Dermoscopy of a skin lesion: 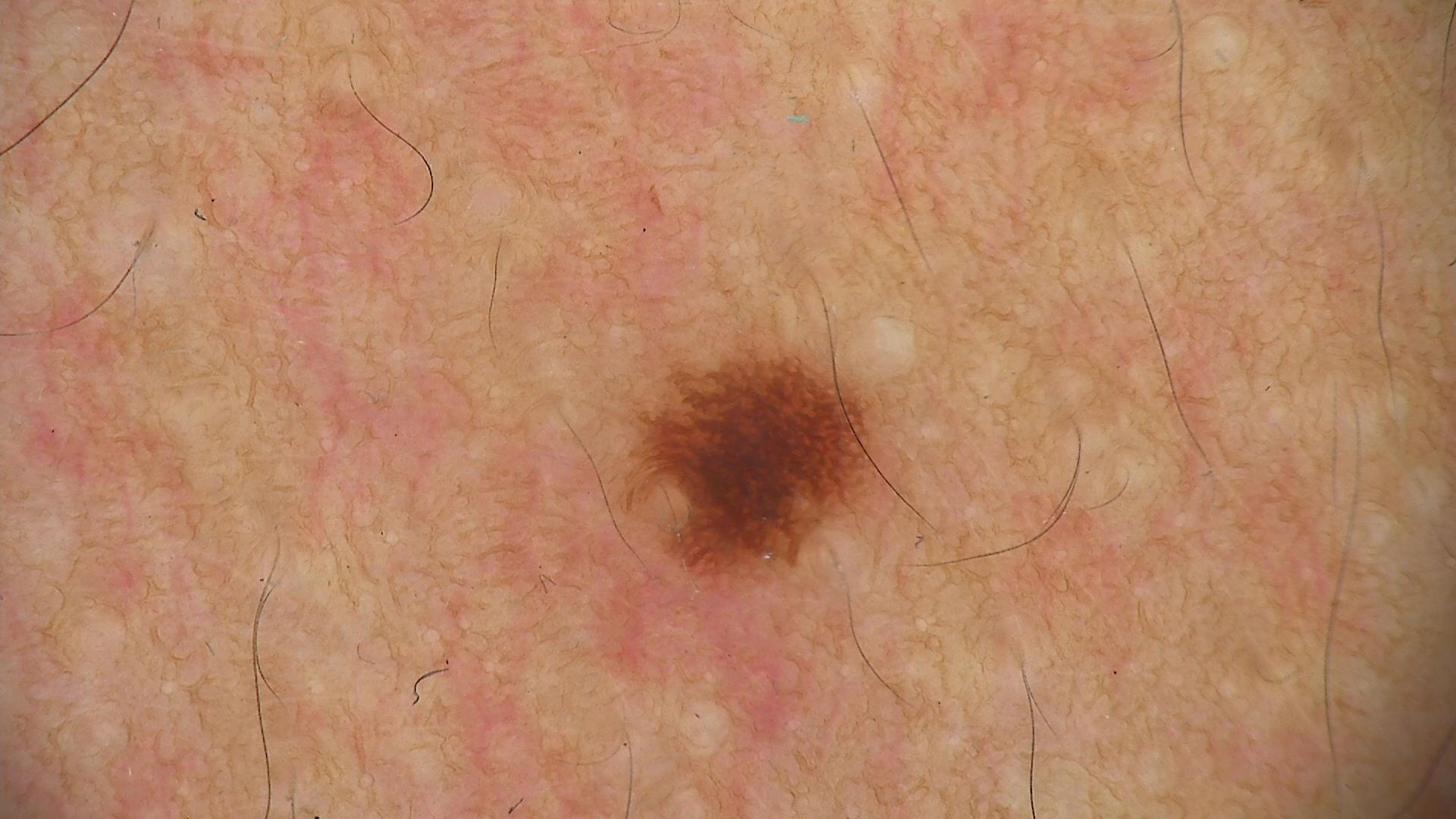| feature | finding |
|---|---|
| class | dysplastic junctional nevus (expert consensus) |